The lesion involves the arm · an image taken at an angle:
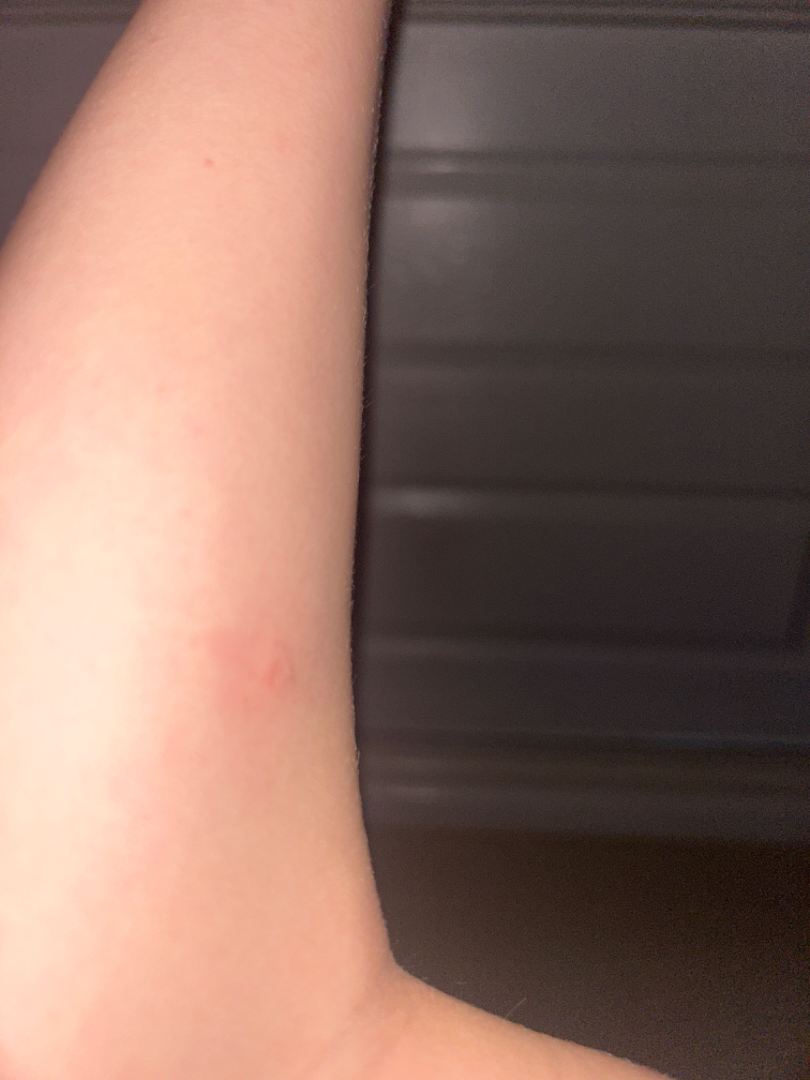The condition could not be reliably identified from the image.